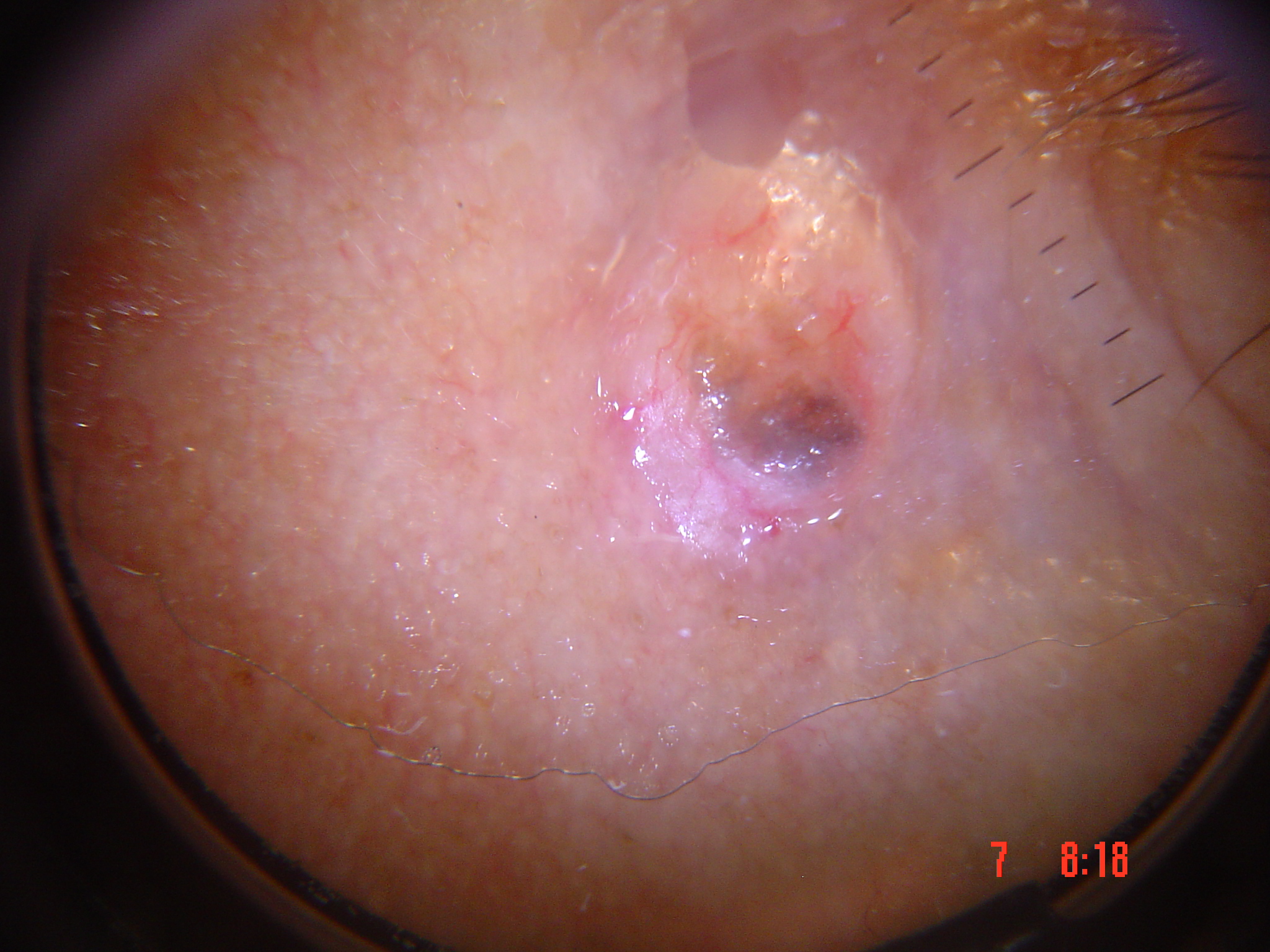A dermoscopic image of a skin lesion.
The morphology is that of a keratinocytic lesion.
Histopathology confirmed a skin cancer — a basal cell carcinoma.